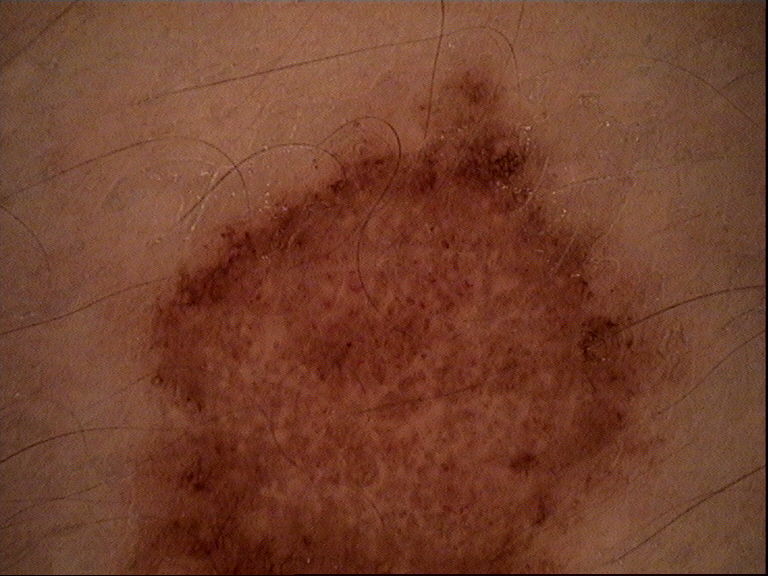Dermoscopy of a skin lesion. The diagnostic label was a dysplastic junctional nevus.